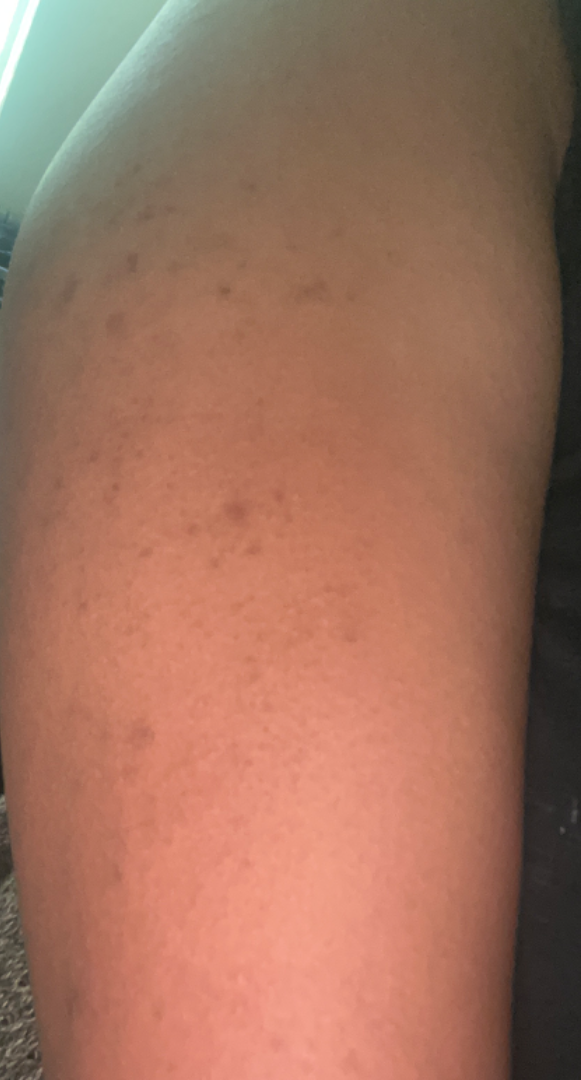History: The patient is a female aged 18–29. The back of the torso, arm and back of the hand are involved. The photo was captured at an angle. Impression: On teledermatology review: Keratosis pilaris (100%).